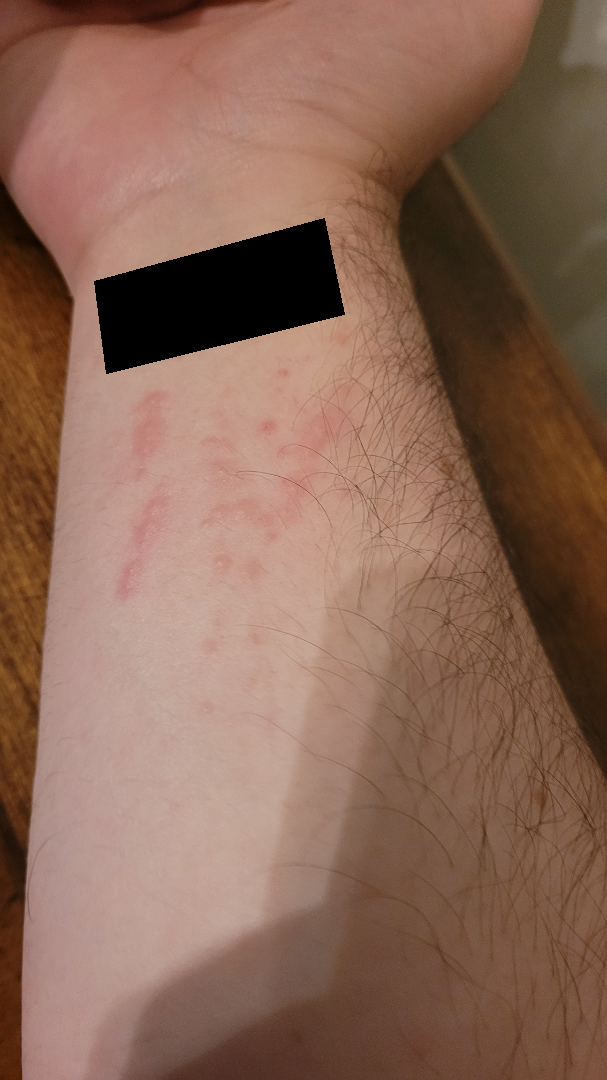| feature | finding |
|---|---|
| assessment | could not be assessed |